Close-up view; female subject, age 50–59.
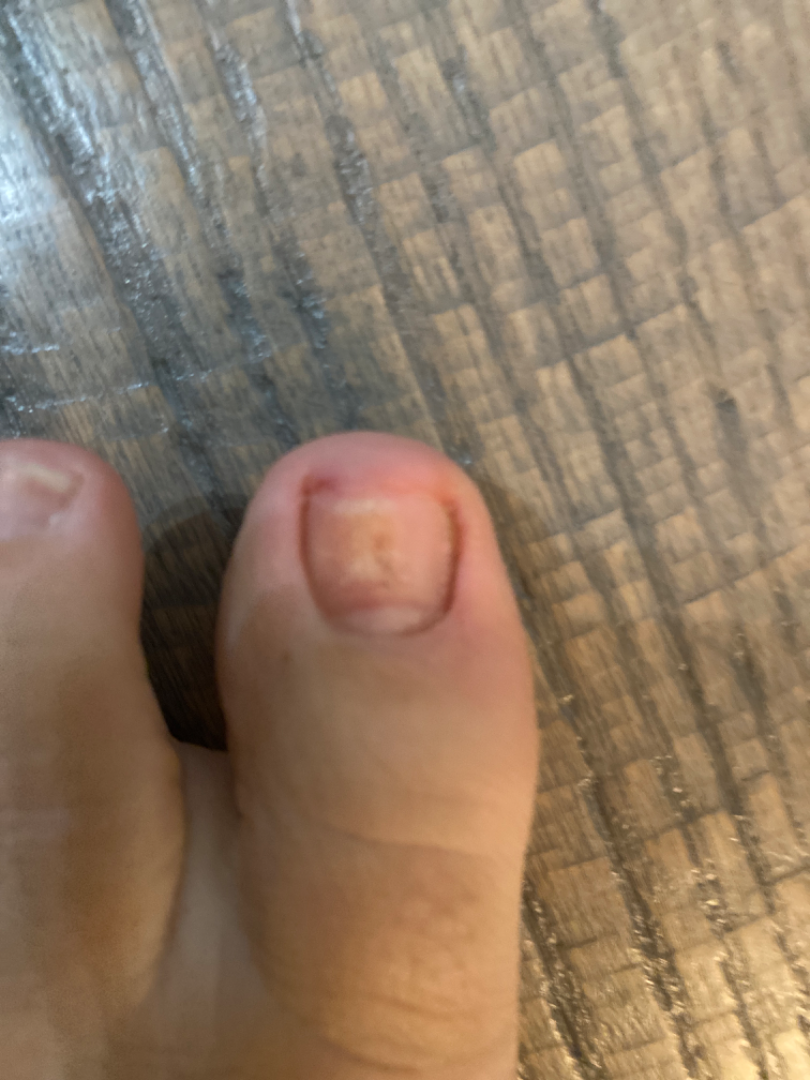described texture: raised or bumpy
patient's own categorization: a nail problem
onset: one to three months
symptoms: bothersome appearance
skin tone: Fitzpatrick III
dermatologist impression: most likely Onychodystrophy; possibly Onychomycosis